The lesion involves the arm, leg and head or neck · this is a close-up image:
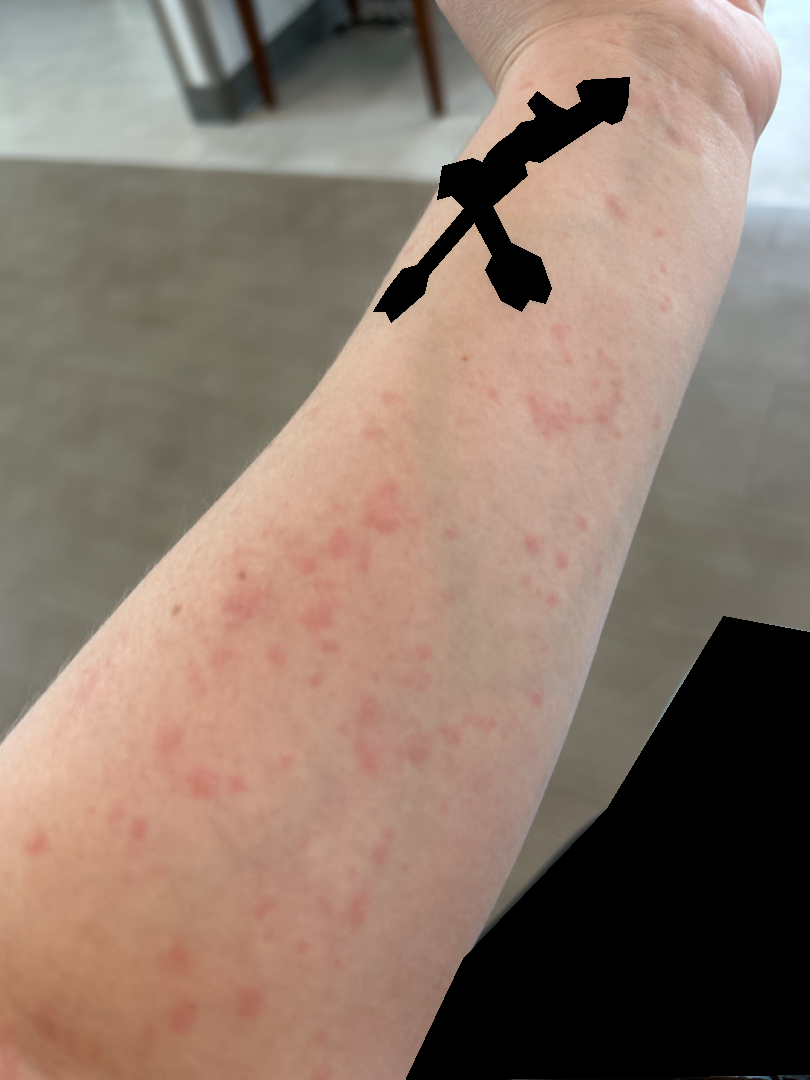assessment: could not be assessed